Close-up view; the lesion involves the palm; female patient, age 18–29.
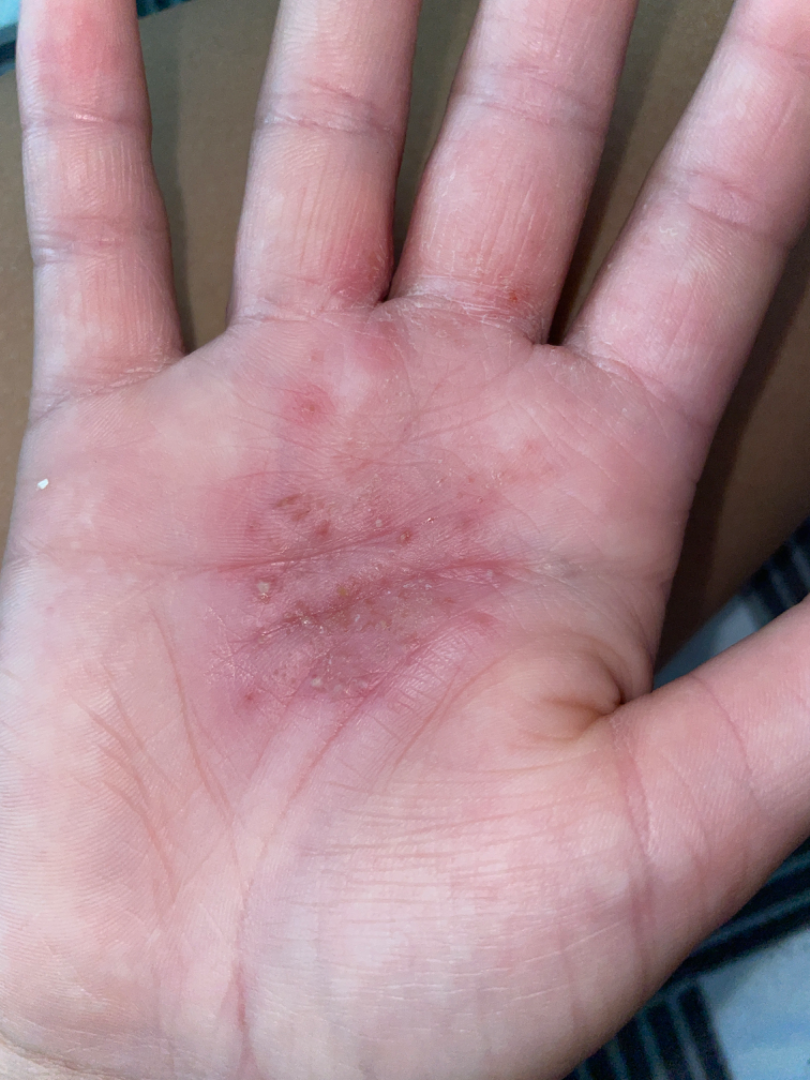Background: Present for less than one week. The lesion is associated with burning, itching and pain. The contributor reports the lesion is rough or flaky and raised or bumpy. Self-categorized by the patient as a rash. Findings: The leading consideration is Eczema; also on the differential is Psoriasis; less likely is Allergic Contact Dermatitis; less probable is Tinea.